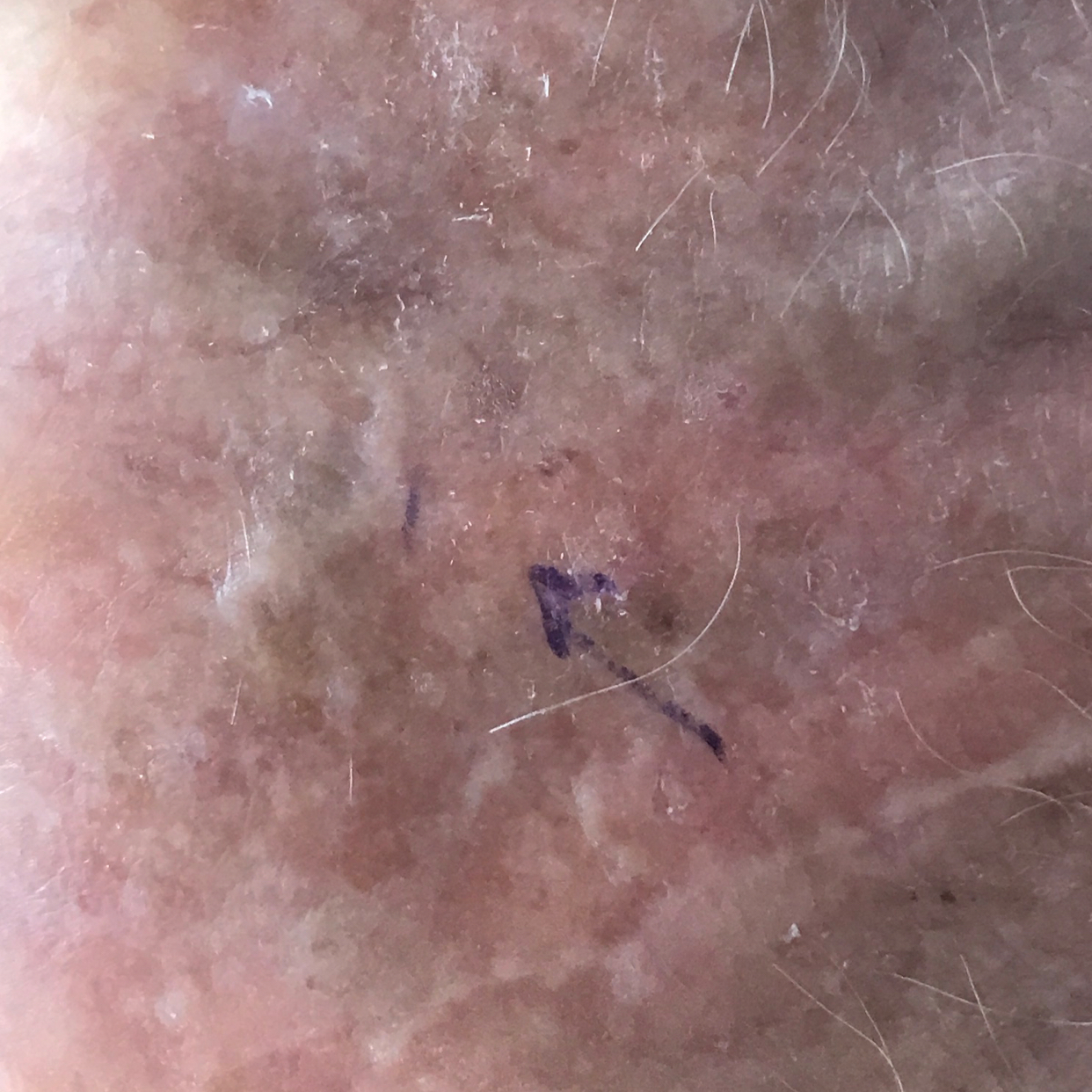| field | value |
|---|---|
| assessment | actinic keratosis (clinical consensus) |